The affected area is the back of the hand. A close-up photograph — 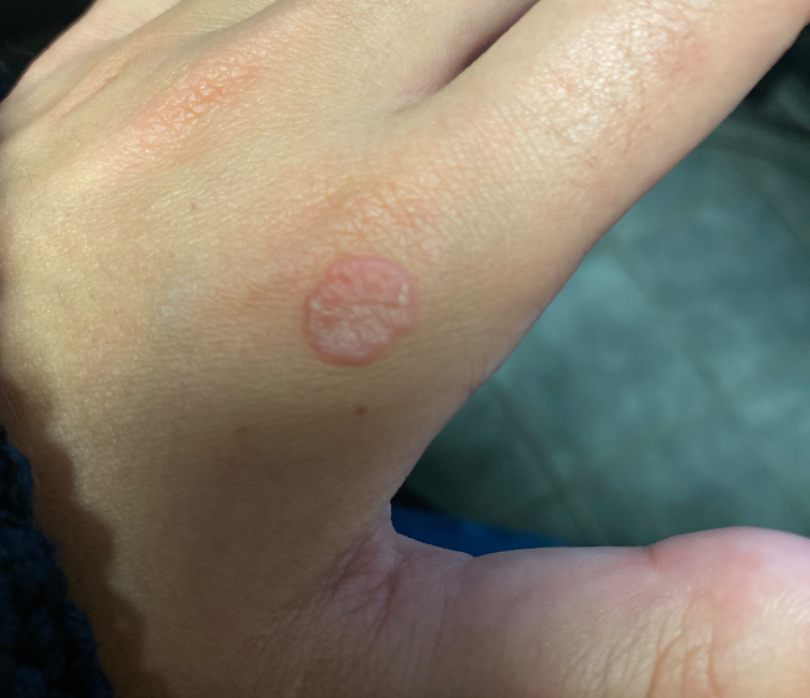Most consistent with Verruca vulgaris; with consideration of Granuloma annulare; possibly Lichen planus/lichenoid eruption.